A dermoscopy image of a single skin lesion.
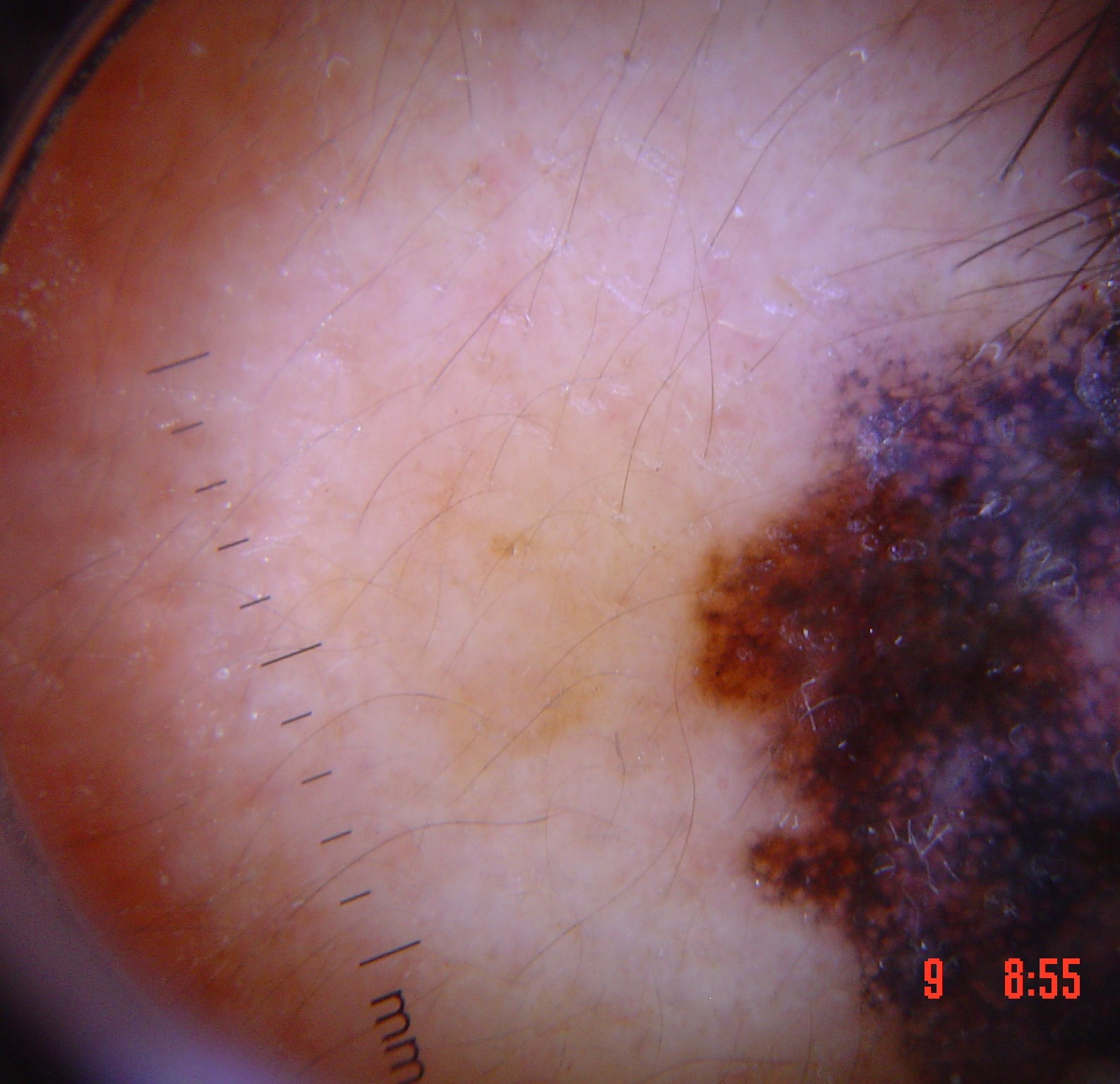class — lentigo maligna (biopsy-proven).